A dermoscopy image of a single skin lesion.
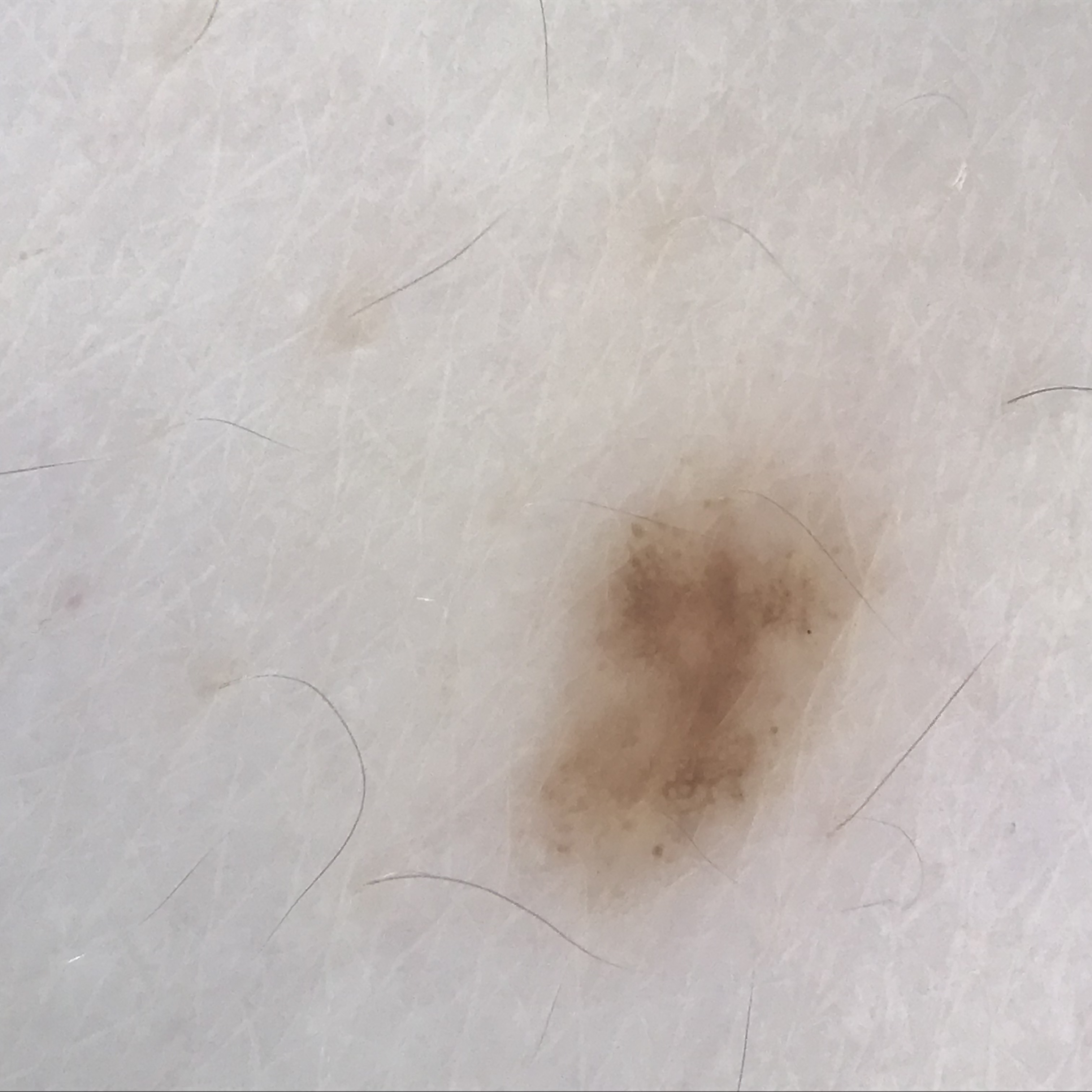Consistent with a benign lesion — a dysplastic junctional nevus.